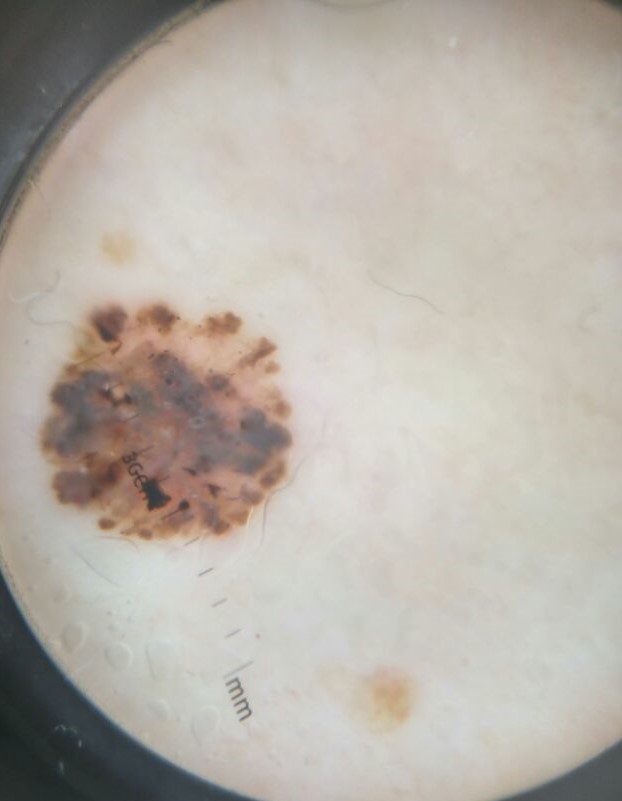Histopathology confirmed a keratinocytic lesion — a basal cell carcinoma.